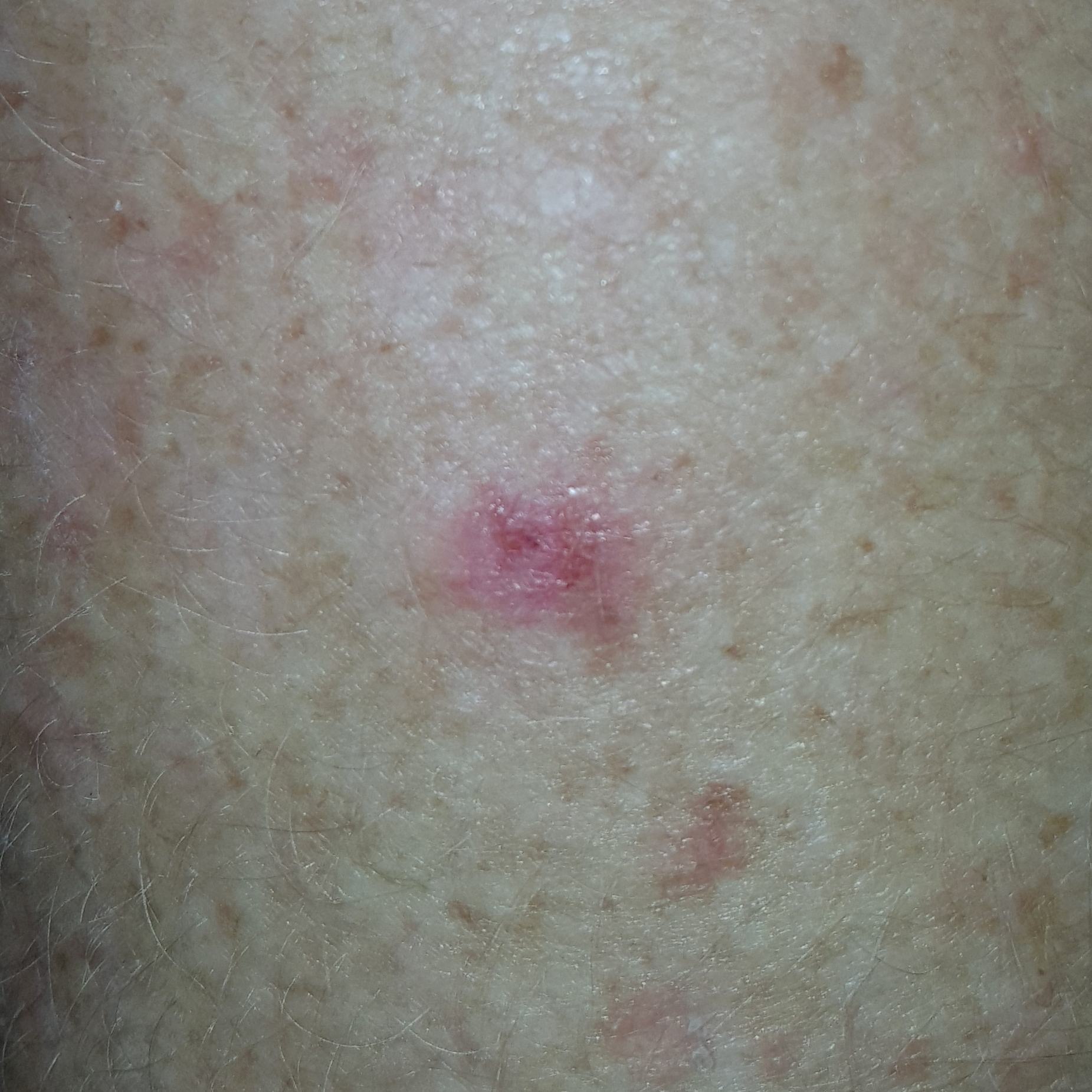A patient 57 years old. A smartphone photograph of a skin lesion. The patient describes that the lesion itches. The diagnostic impression was a premalignant lesion — an actinic keratosis.